A dermatoscopic image of a skin lesion: 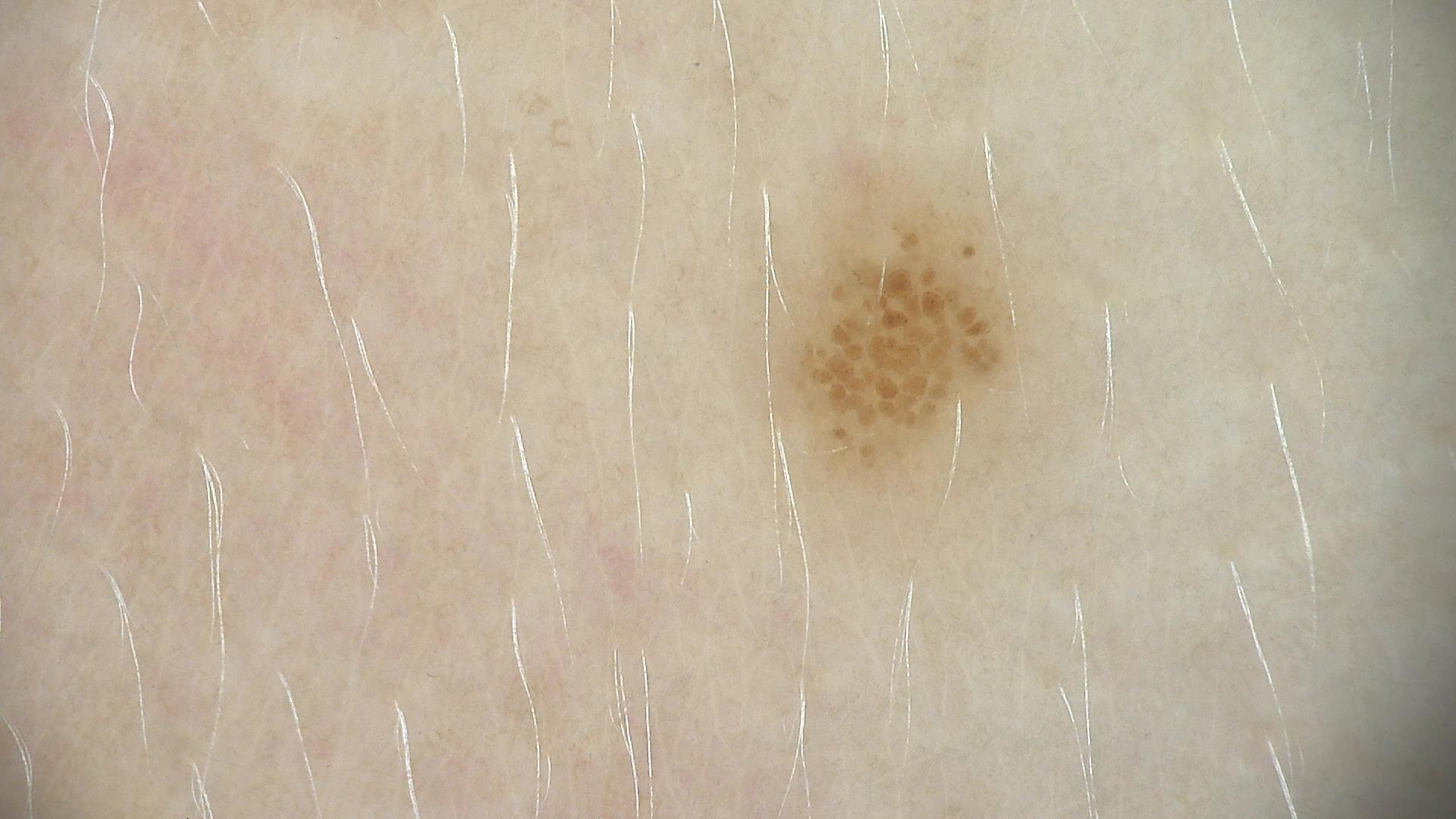{"diagnosis": {"name": "dysplastic junctional nevus", "code": "jd", "malignancy": "benign", "super_class": "melanocytic", "confirmation": "expert consensus"}}